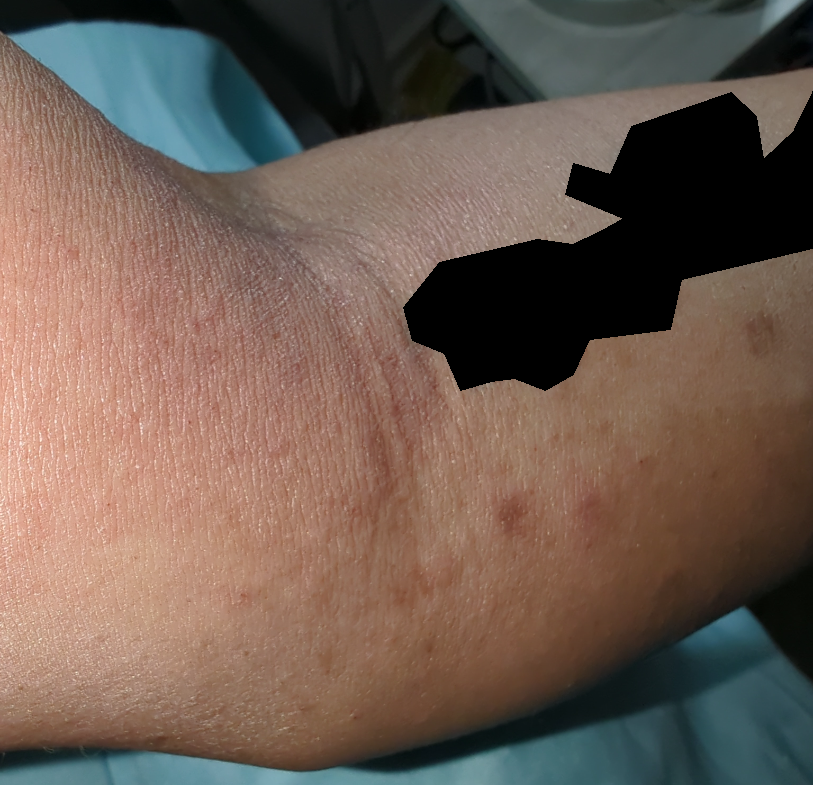Patient information: The lesion involves the arm and front of the torso. A close-up photograph. Review: On photographic review by a dermatologist, the impression is Eczema.